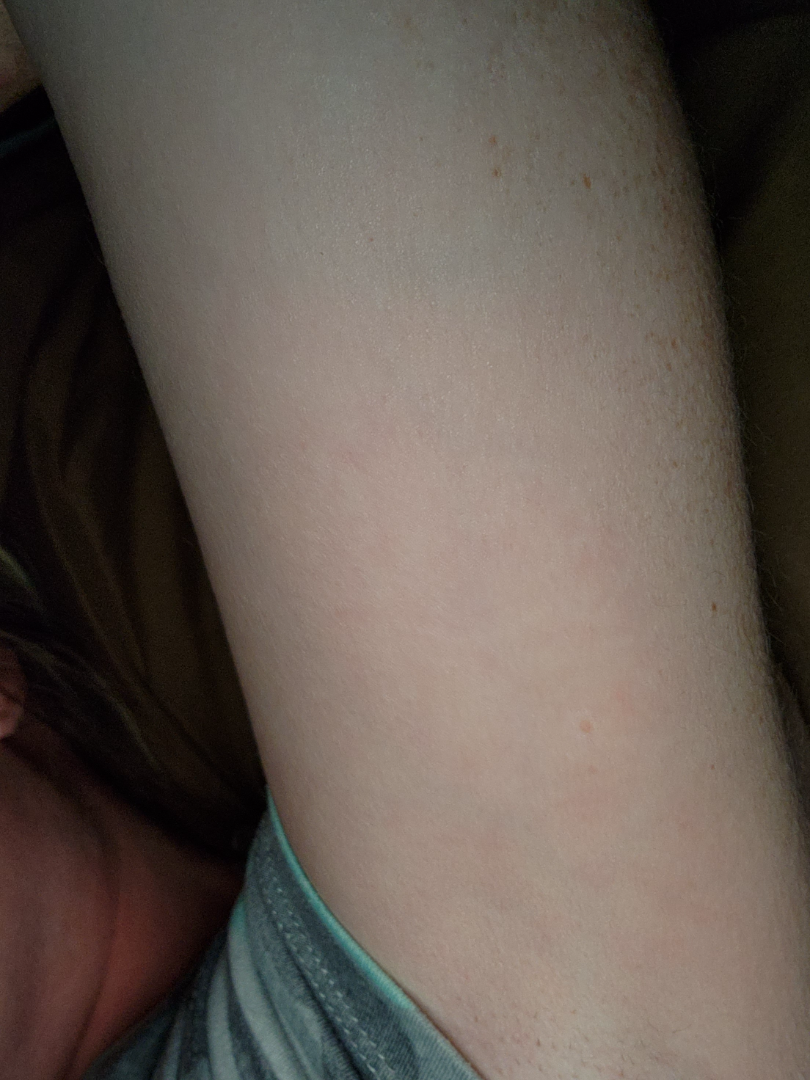| feature | finding |
|---|---|
| assessment | no discernible pathology |